Fitzpatrick II. The chart records prior malignancy (patient or family), pesticide exposure, and prior skin cancer (patient or family). A male subject in their early 50s. A clinical photograph of a skin lesion — 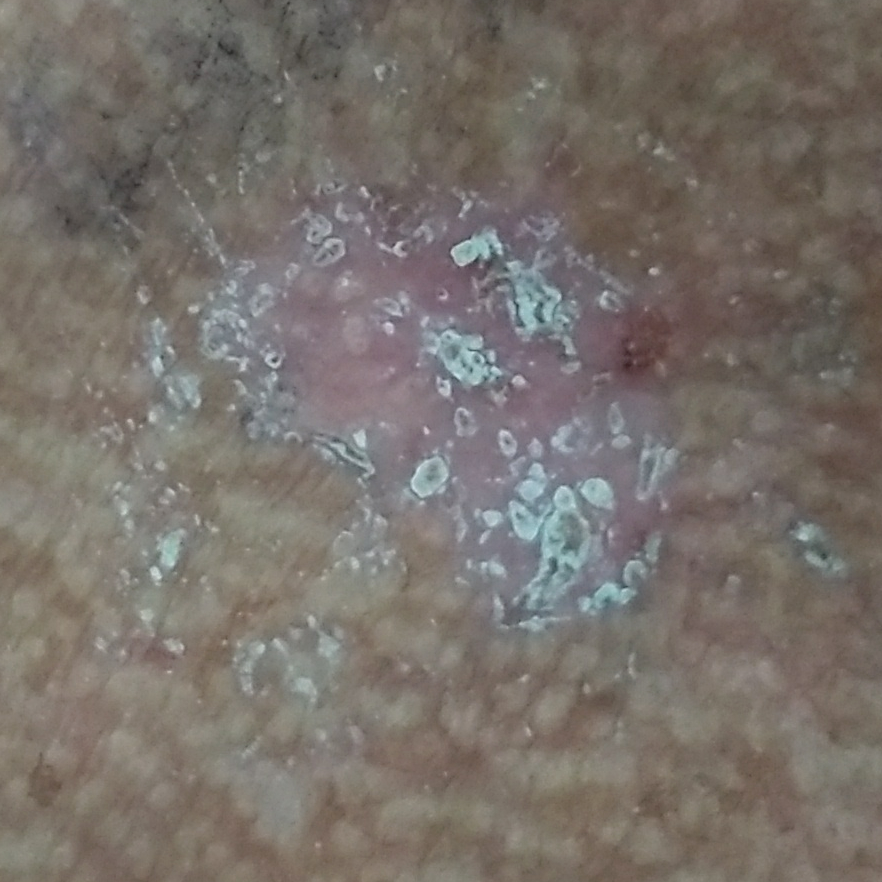anatomic site: the chest | diameter: 35 × 27 mm | reported symptoms: pain, elevation, itching | diagnostic label: basal cell carcinoma (biopsy-proven).